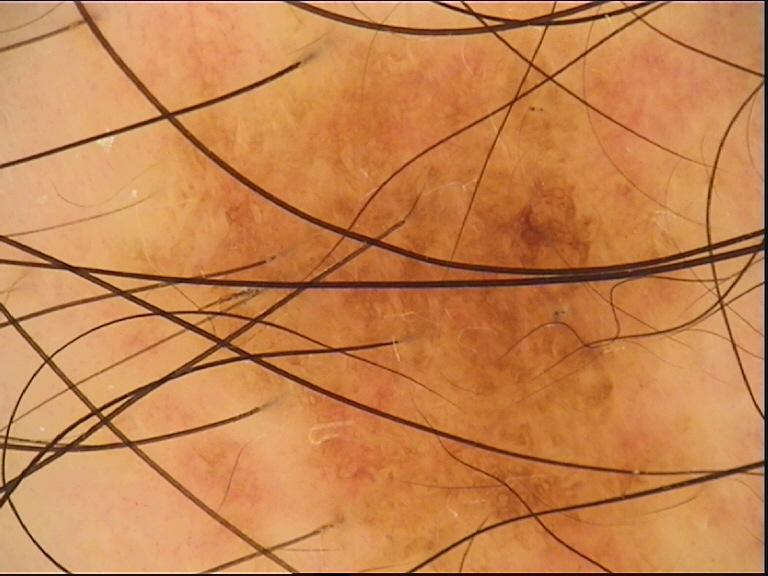Conclusion: Diagnosed as a dysplastic compound nevus.